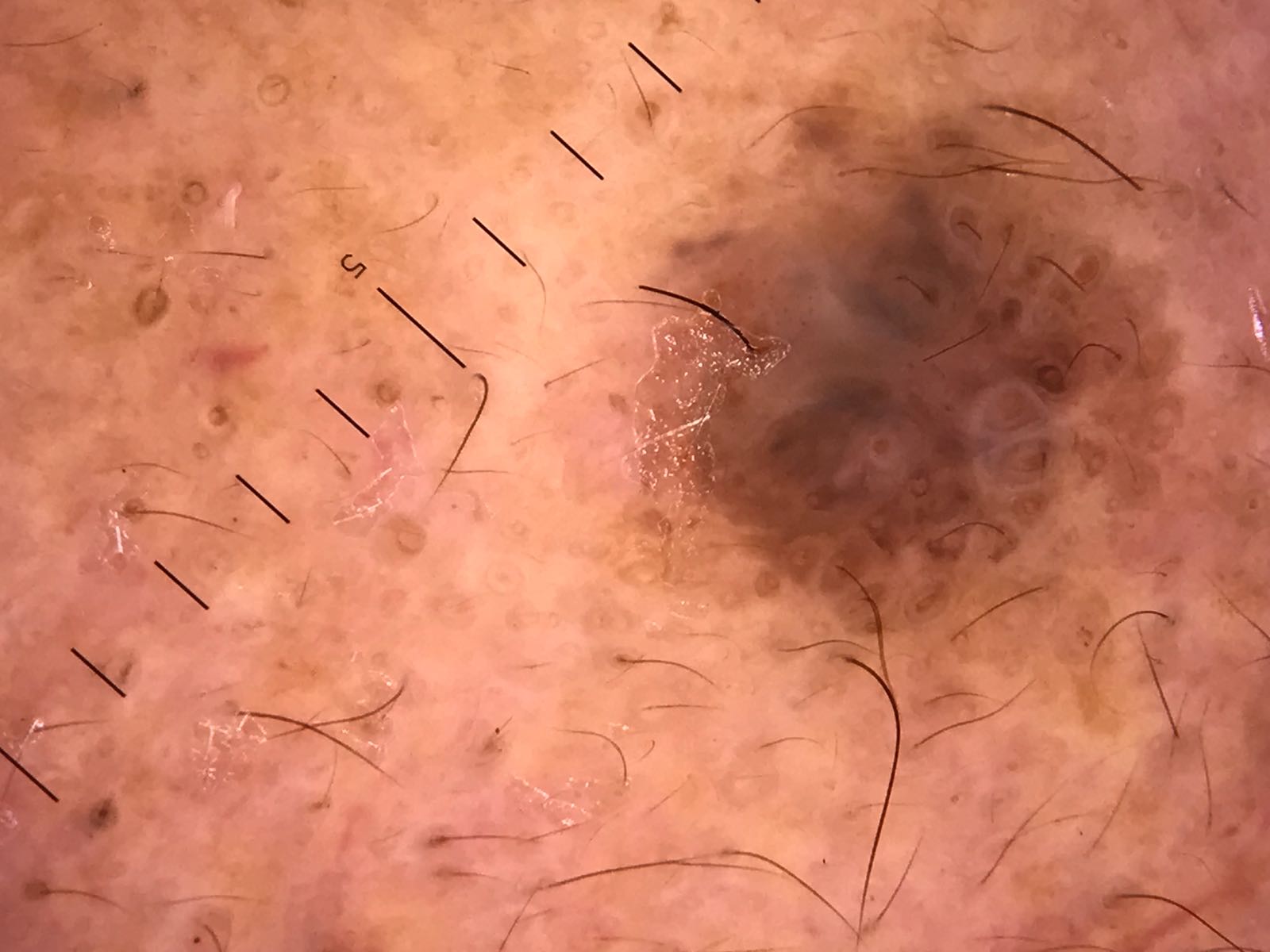diagnostic label = seborrheic keratosis (expert consensus)